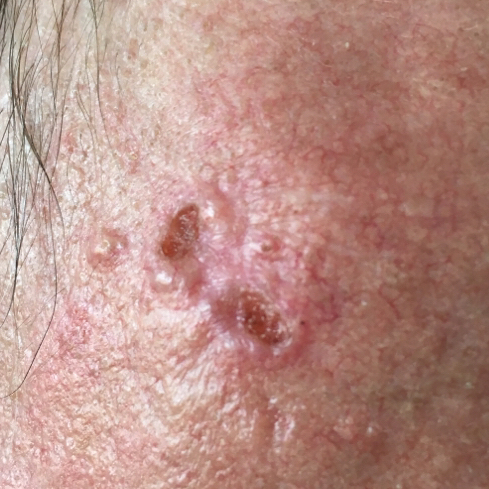Q: What is the patient's skin type?
A: II
Q: What is the imaging modality?
A: clinical photograph
Q: Any relevant history?
A: prior skin cancer (patient or family), pesticide exposure, no tobacco use
Q: Where on the body is the lesion?
A: the face
Q: Lesion size?
A: 10 × 4 mm
Q: What does the patient describe?
A: itching, bleeding, elevation / no pain
Q: What is this lesion?
A: basal cell carcinoma (biopsy-proven)